Dermoscopy of a skin lesion. A female patient aged 53 to 57. Skin type II — 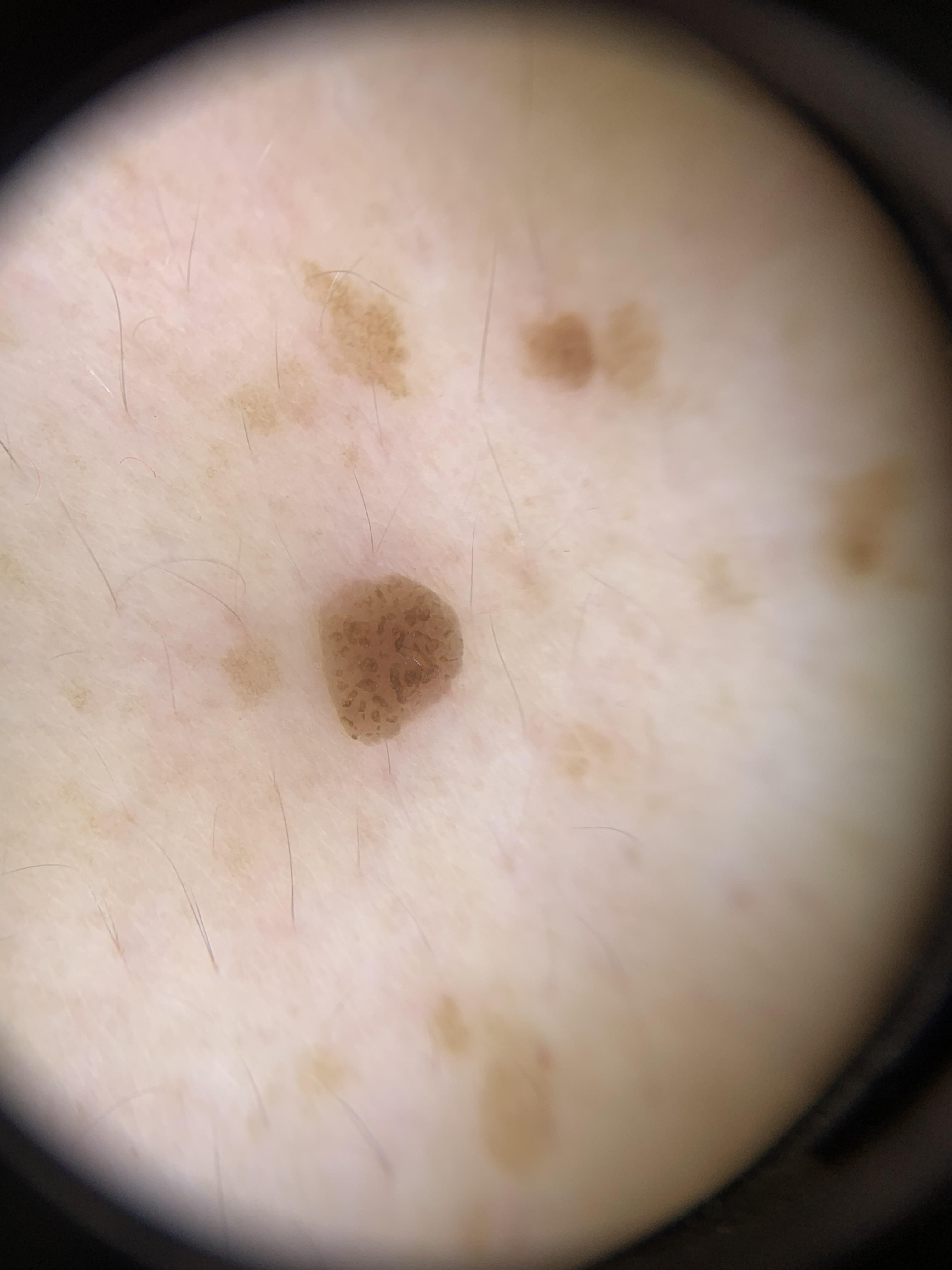Image and clinical context: The lesion involves the trunk. Assessment: Consistent with a benign lesion — a seborrheic keratosis.